A male subject, in their 40s. A dermoscopic close-up of a skin lesion.
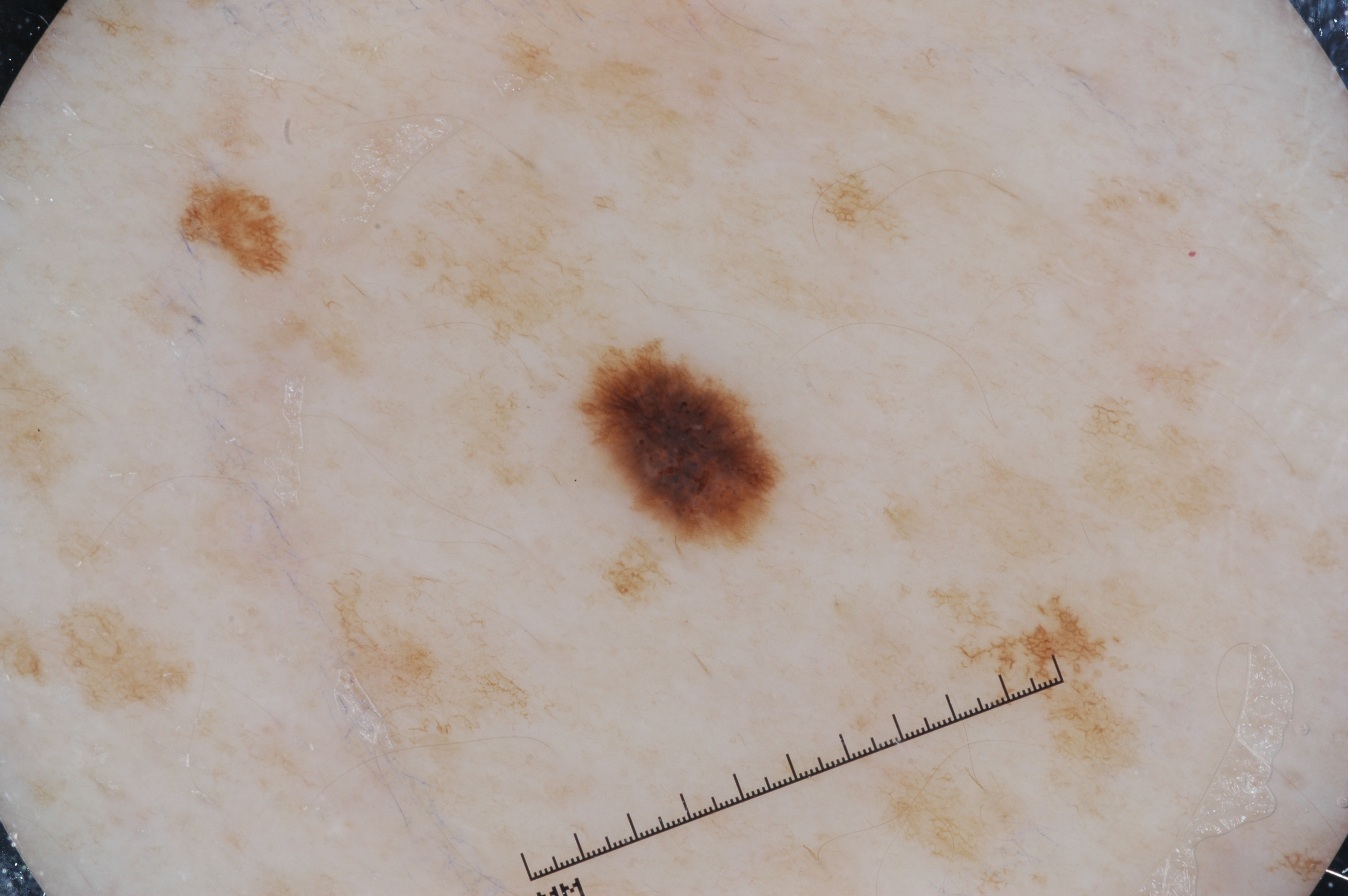Dermoscopy demonstrates pigment network, with no milia-like cysts, streaks, or negative network. The lesion spans 590, 350, 779, 539. Diagnosed as a melanocytic nevus, a benign skin lesion.